The lesion involves the head or neck, leg, back of the hand and arm. This image was taken at a distance — 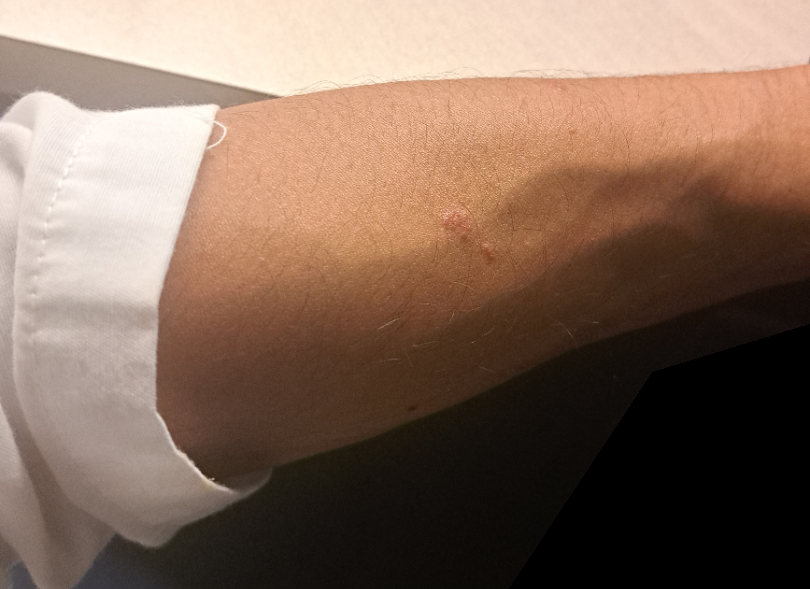- assessment · ungradable on photographic review